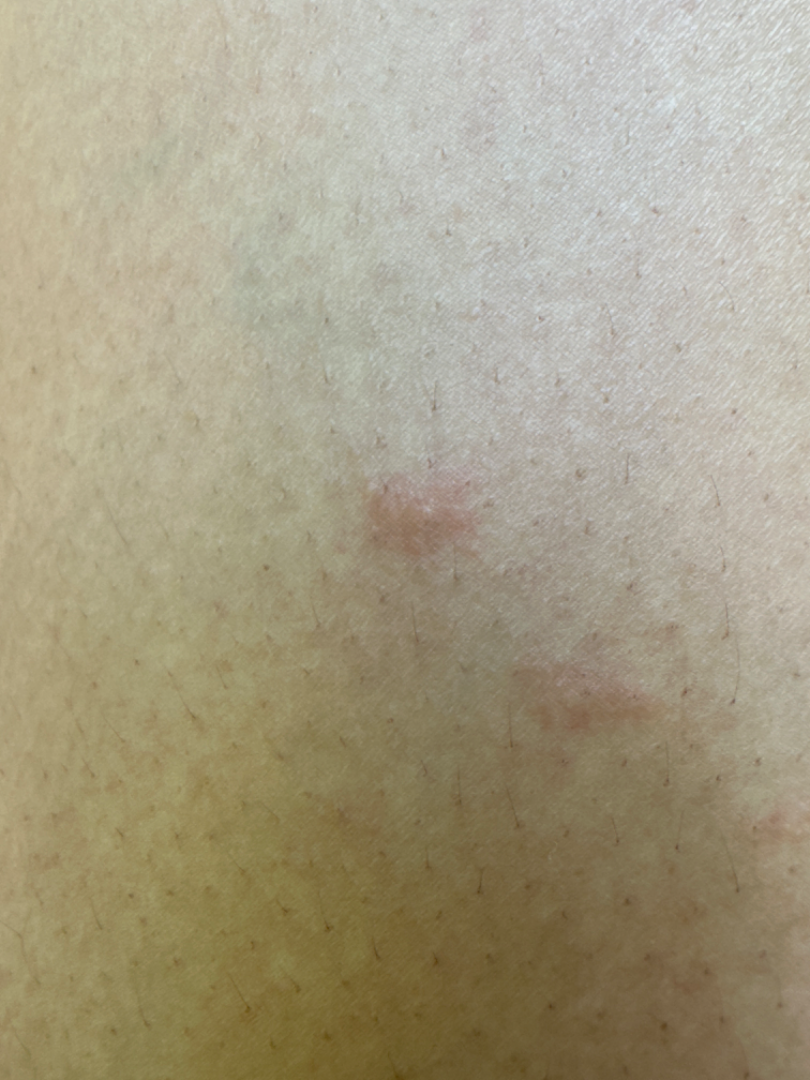The photograph is a close-up of the affected area.
Single-reviewer assessment: most consistent with Insect Bite; possibly Allergic Contact Dermatitis; a remote consideration is Urticaria.